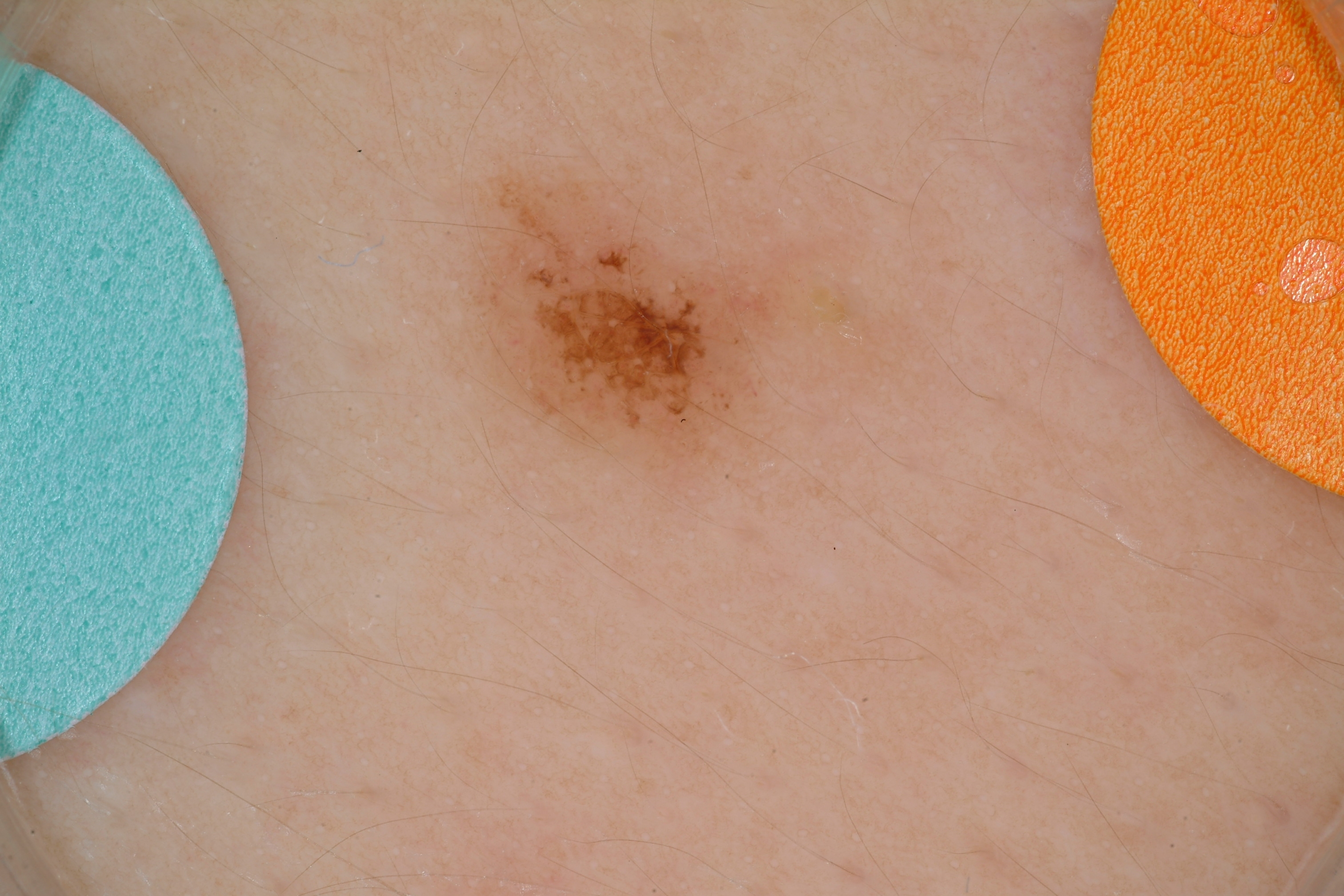Case summary:
A skin lesion imaged with a dermatoscope. Dermoscopic review identifies globules, with no streaks. As (left, top, right, bottom), the lesion's extent is (466, 144, 765, 475).
Conclusion:
Expert review diagnosed this as a benign skin lesion.